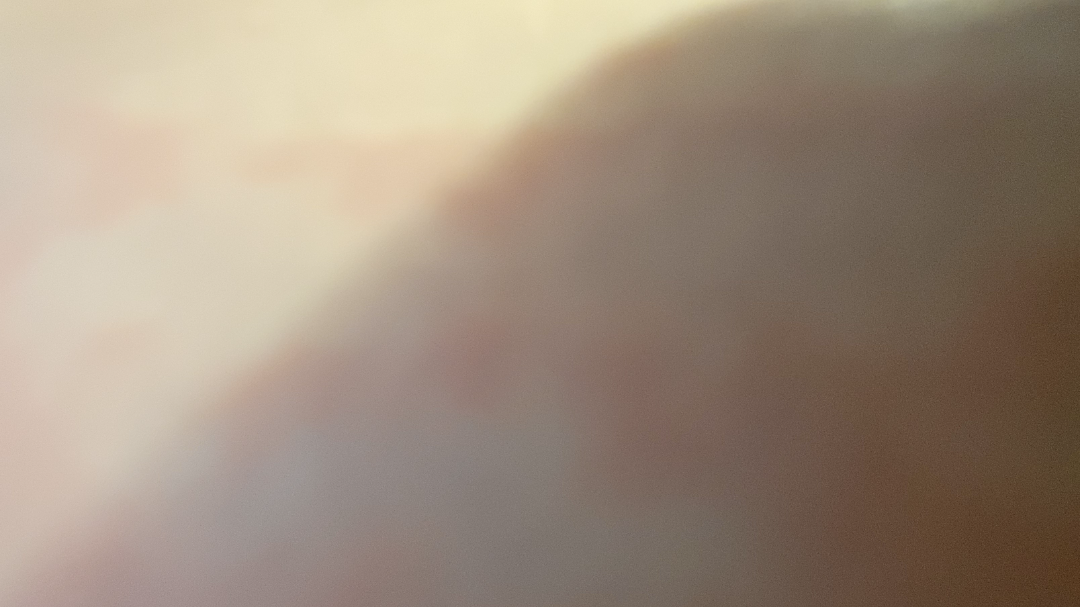Review:
The reviewing dermatologist was unable to assign a differential diagnosis from the image.
Patient information:
Symptoms reported: darkening, burning, bothersome appearance, pain, itching and enlargement. No relevant systemic symptoms. The patient considered this a rash. The subject is female. The lesion involves the arm, front of the torso, back of the torso, leg and head or neck. An image taken at an angle.